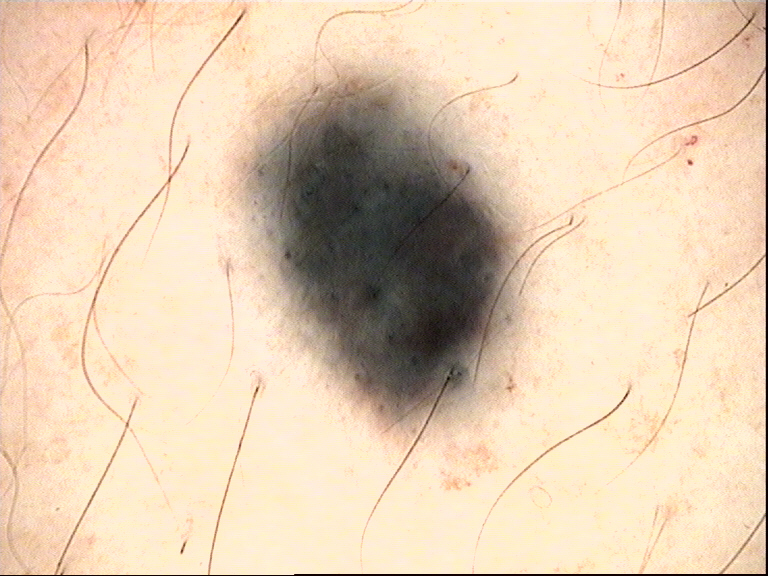diagnostic label=blue nevus (expert consensus).